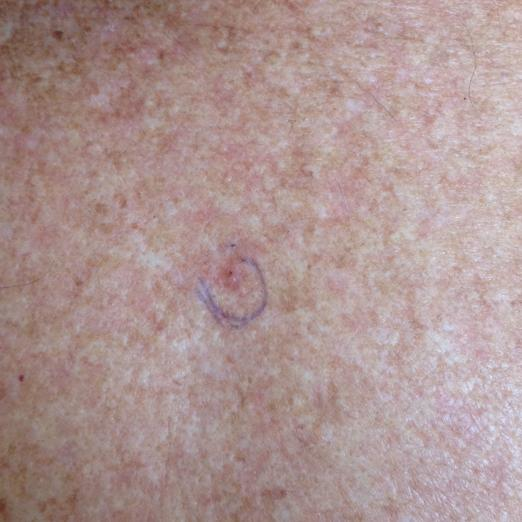Findings:
A patient in their early 50s. Located on the back. The patient reports that the lesion itches, but has not changed.
Conclusion:
The clinical impression was an actinic keratosis.